Male contributor, age 18–29 · an image taken at a distance · the lesion involves the arm, head or neck and front of the torso — 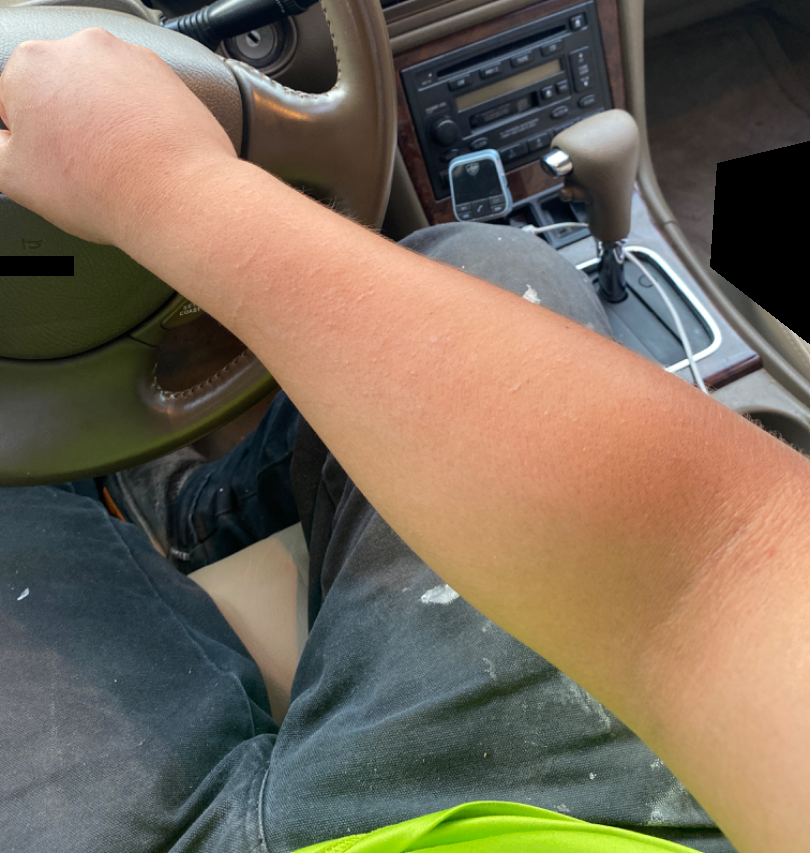Skin tone: Fitzpatrick II. The patient indicates the condition has been present for less than one week. The patient described the issue as a rash. Texture is reported as raised or bumpy. The patient indicates burning, itching and darkening. The reviewing dermatologists' impression was: Photodermatitis (0.30); Urticaria (0.23); Allergic Contact Dermatitis (0.23); Irritant Contact Dermatitis (0.15); Eczema (0.10).